A smartphone photograph of a skin lesion; a subject in their 60s:
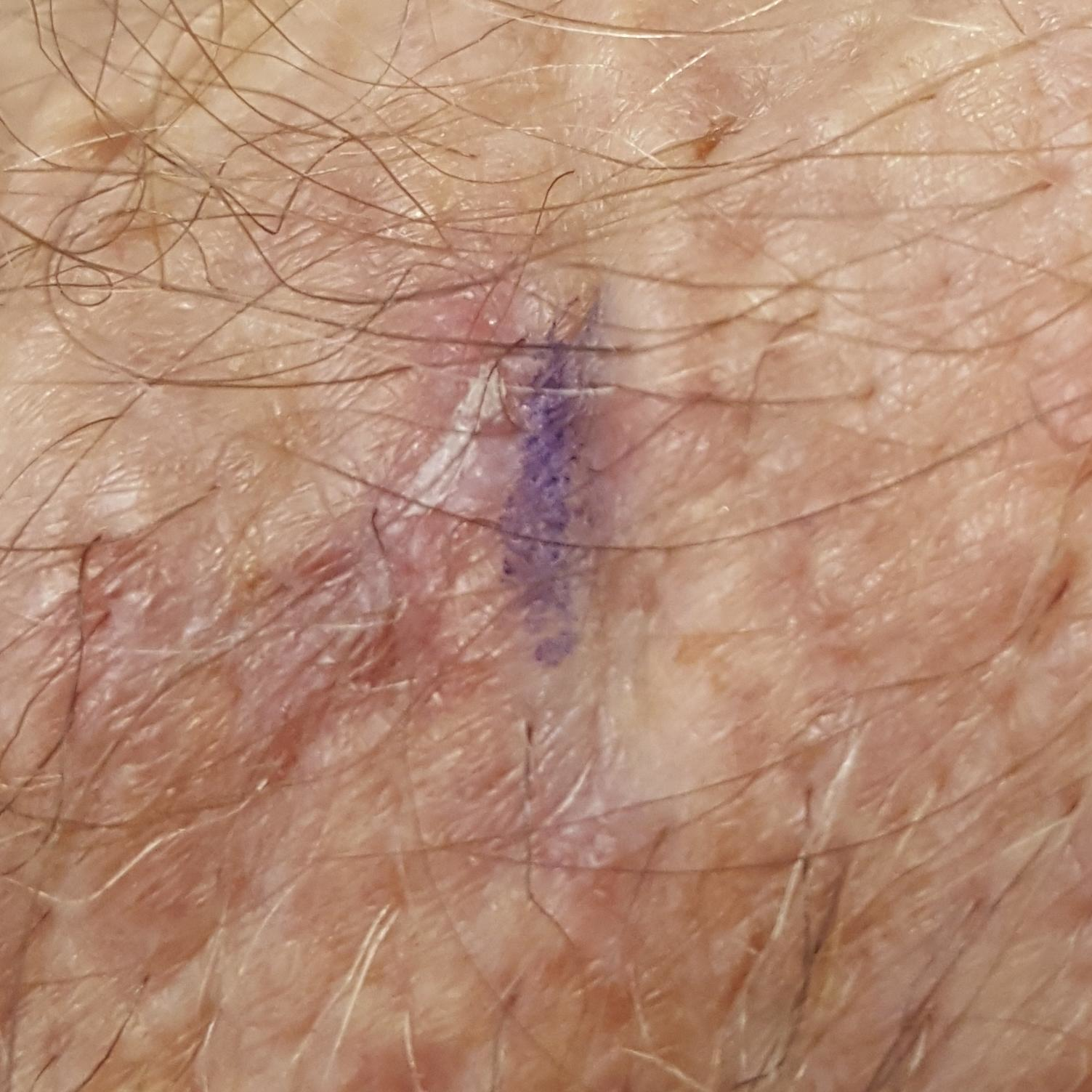Findings:
Located on a forearm. By the patient's account, the lesion itches and is elevated.
Impression:
Clinically diagnosed as a lesion with uncertain malignant potential — an actinic keratosis.